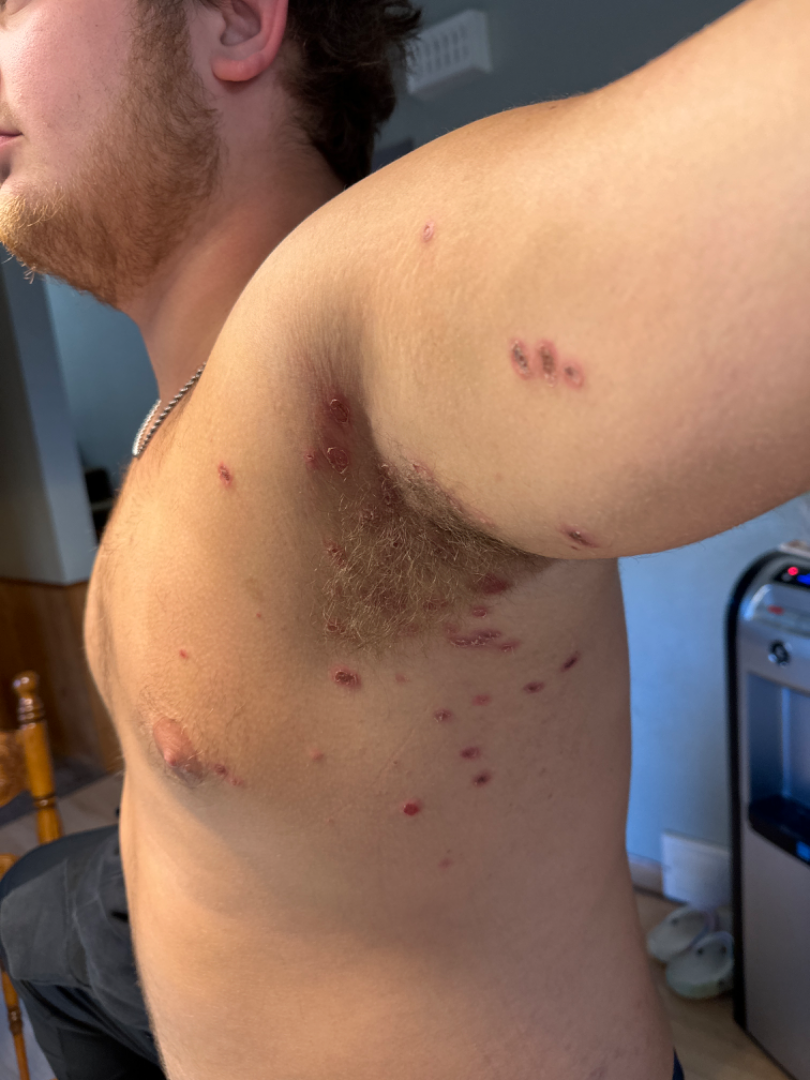Q: What conditions are considered?
A: in keeping with Impetigo